A dermoscopic image of a skin lesion; a female subject, roughly 45 years of age:
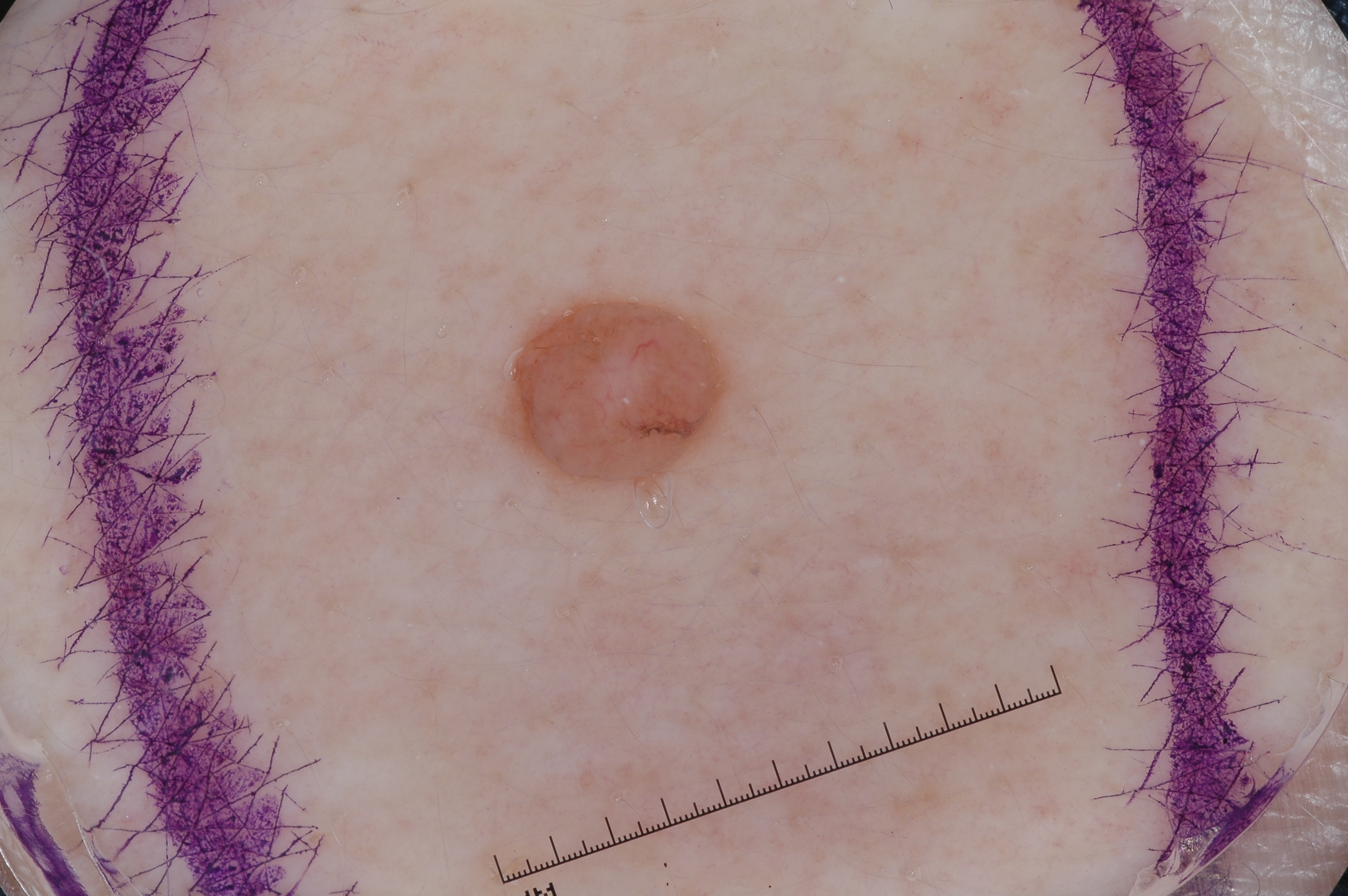  lesion_location:
    bbox_xyxy:
      - 495
      - 294
      - 737
      - 497
  dermoscopic_features:
    present: []
    absent:
      - pigment network
      - streaks
      - milia-like cysts
      - negative network
  lesion_extent:
    approx_field_fraction_pct: 3
  diagnosis:
    name: melanocytic nevus
    malignancy: benign
    lineage: melanocytic
    provenance: clinical